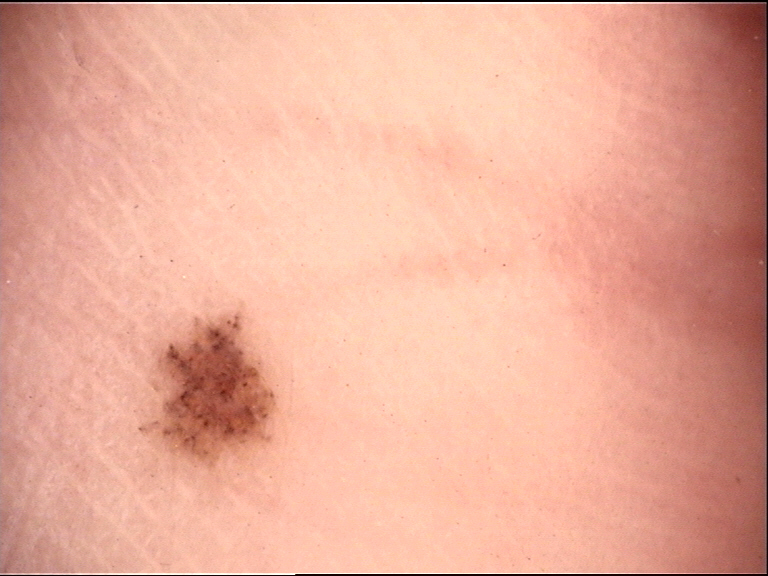Findings:
- label: acral junctional nevus (expert consensus)